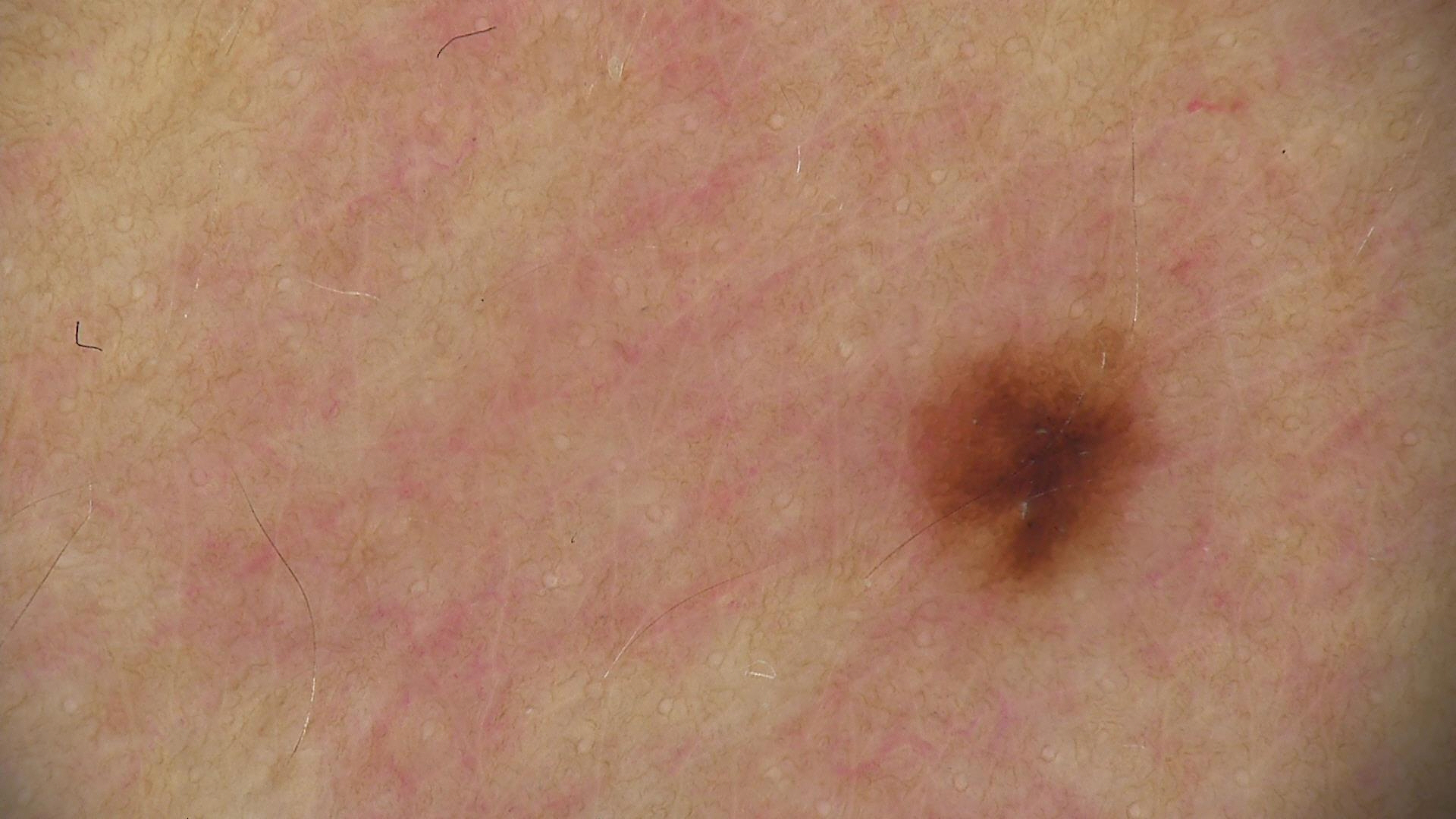A dermoscopic photograph of a skin lesion.
Classified as a dysplastic junctional nevus.